Close-up view, the leg and top or side of the foot are involved — 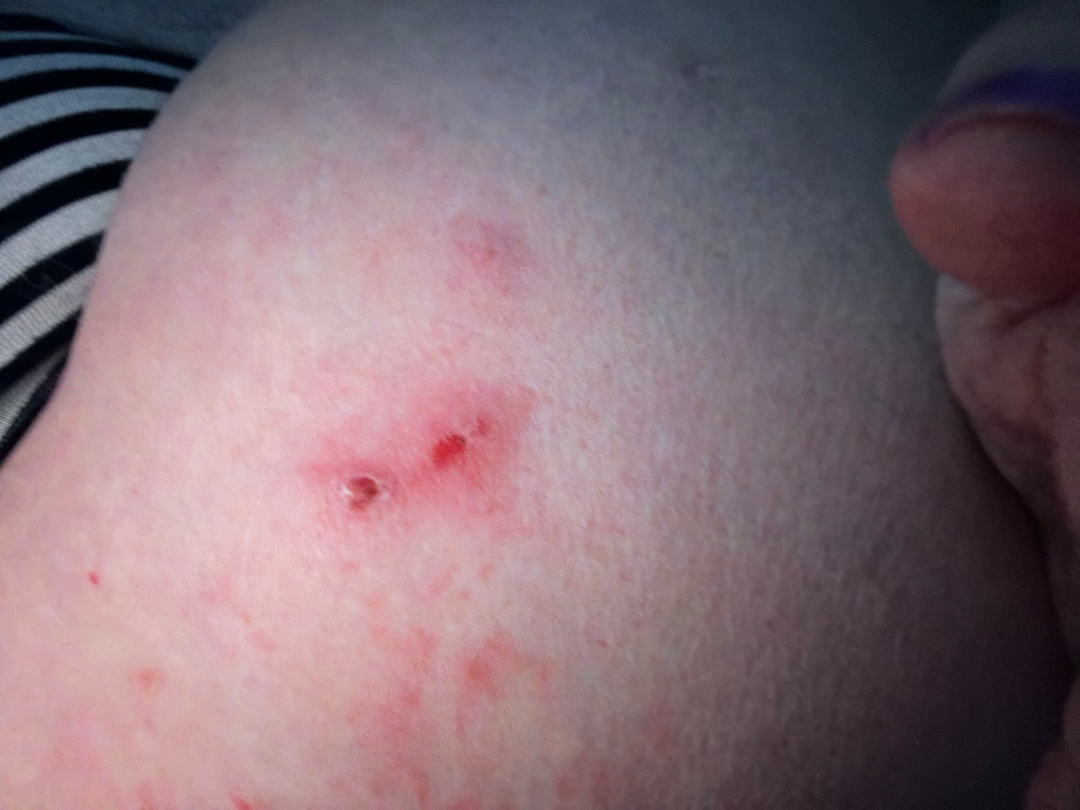The patient reports burning, bothersome appearance, itching, bleeding, pain, enlargement and darkening.
Present for one to three months.
Self-categorized by the patient as skin that appeared healthy to them.
Texture is reported as raised or bumpy and fluid-filled.
A single dermatologist reviewed the case: in keeping with Eczema.